A dermatoscopic image of a skin lesion: 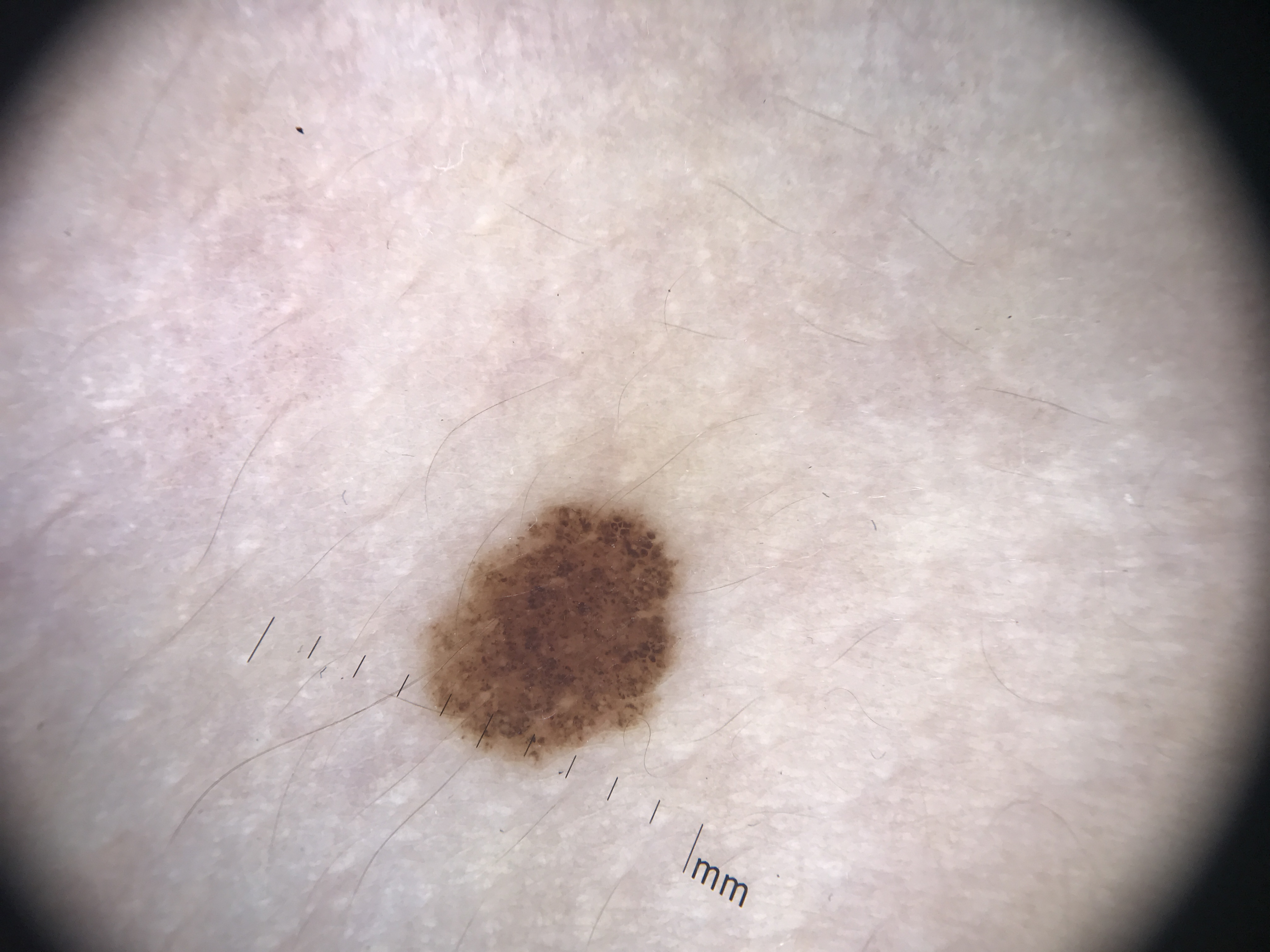Q: What is the diagnosis?
A: dysplastic junctional nevus (expert consensus)